A dermoscopic close-up of a skin lesion:
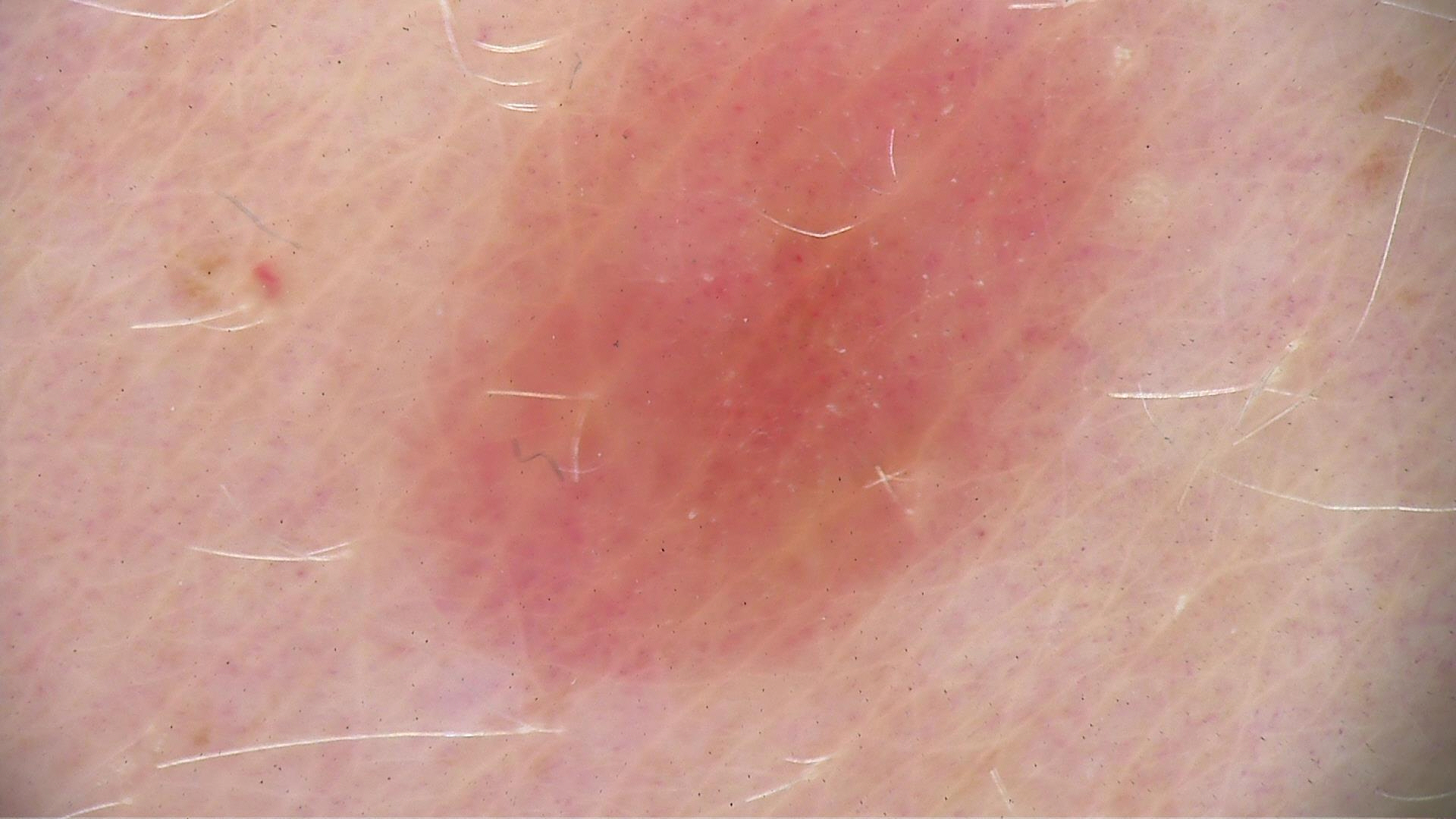class: dysplastic junctional nevus (expert consensus).